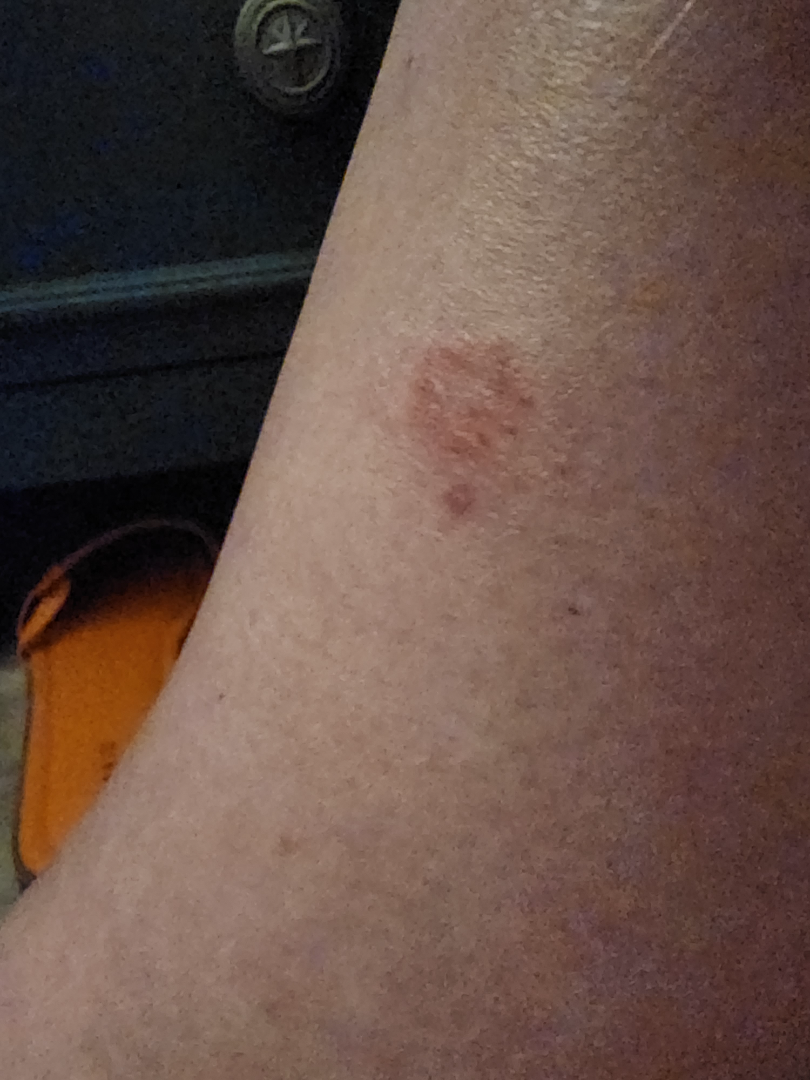| key | value |
|---|---|
| differential | three dermatologists each reviewed the case: Tinea and Eczema were considered with similar weight; less likely is Pityriasis rosea |